A skin lesion imaged with a dermatoscope; the patient is FST II:
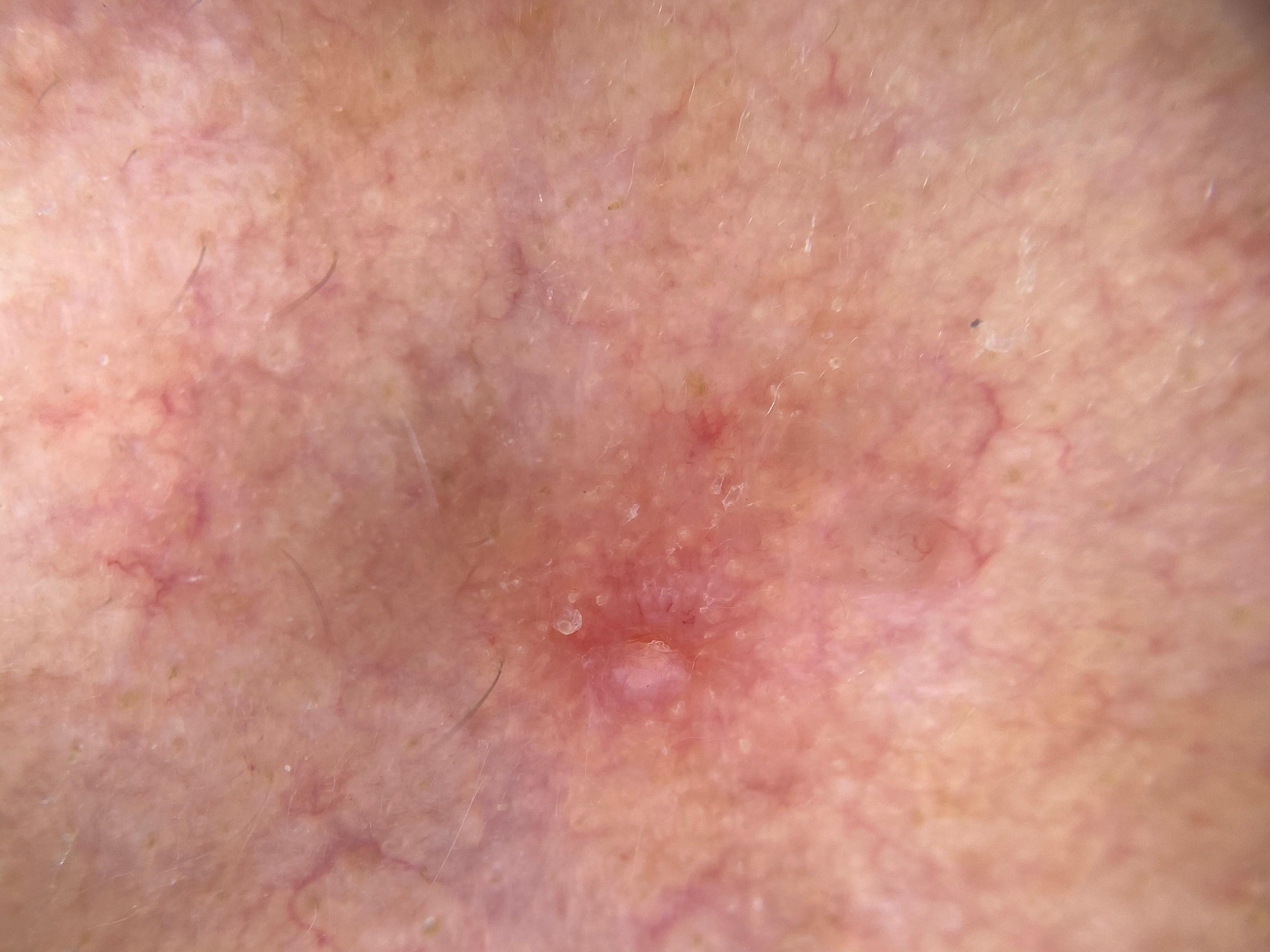Located on the head or neck. Biopsy-confirmed as a malignant lesion — a basal cell carcinoma.